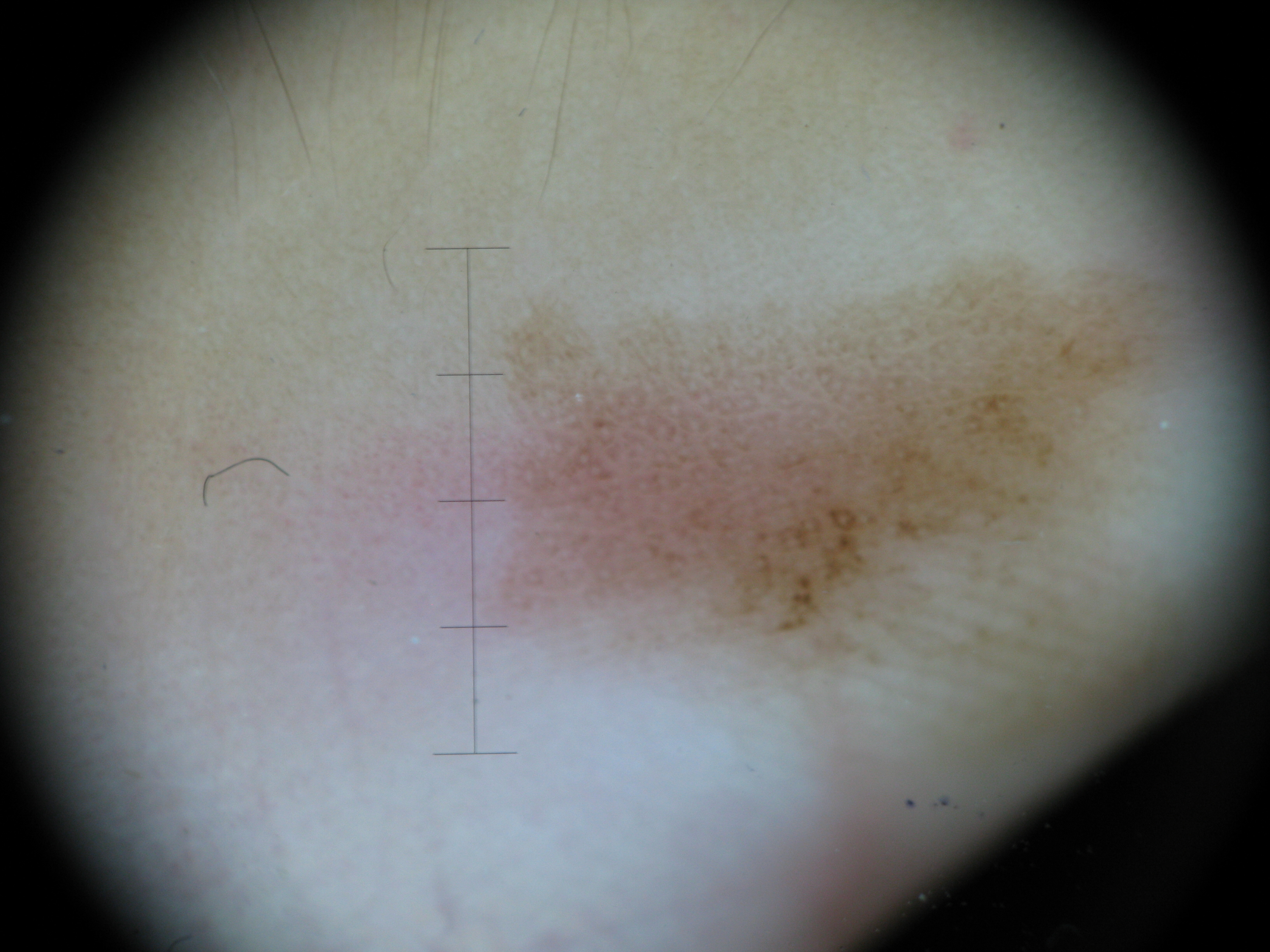Case:
A dermatoscopic image of a skin lesion. This is a banal lesion.
Impression:
The diagnosis was an acral junctional nevus.